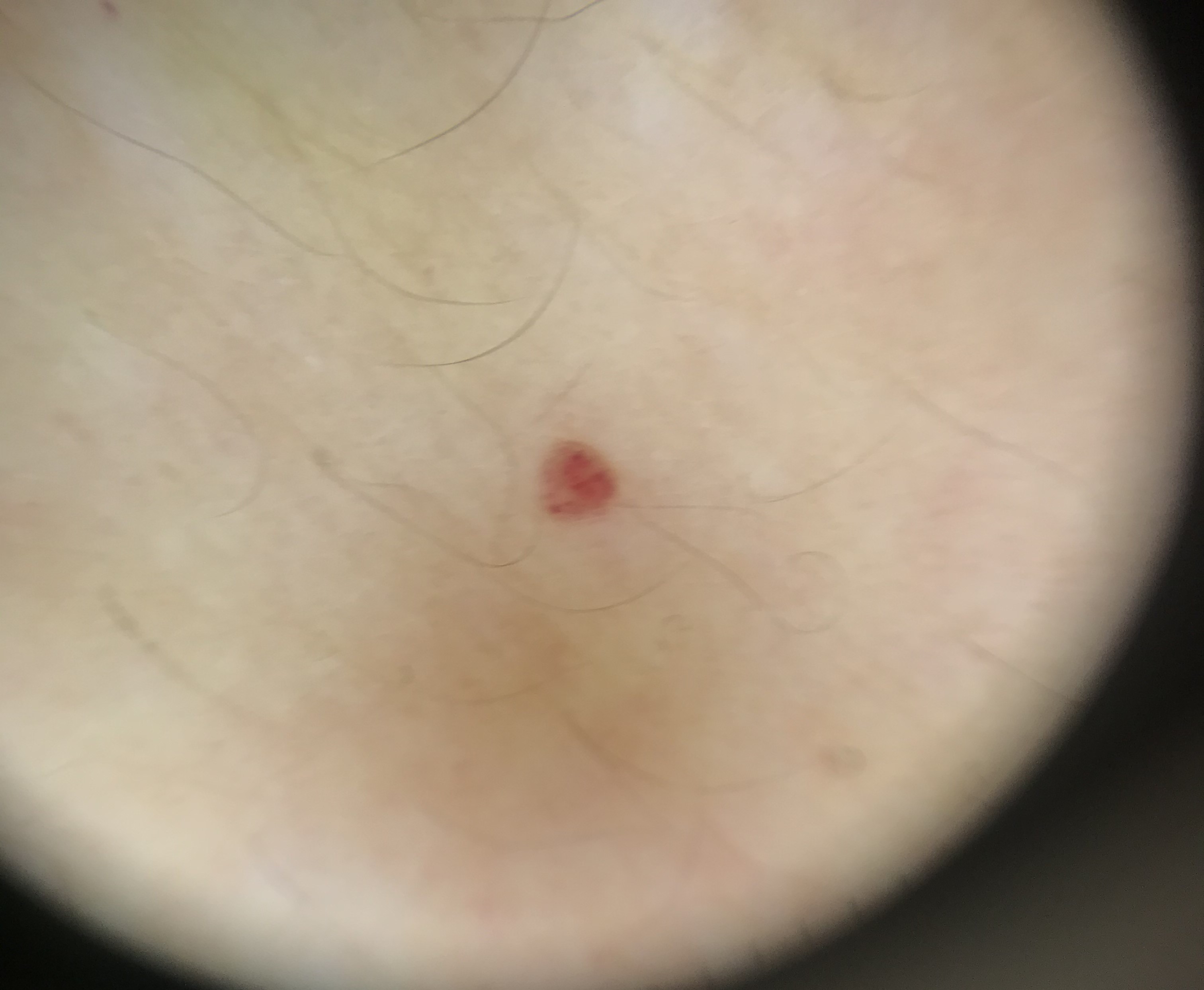image = dermatoscopy | subtype = vascular | label = hemangioma (expert consensus).